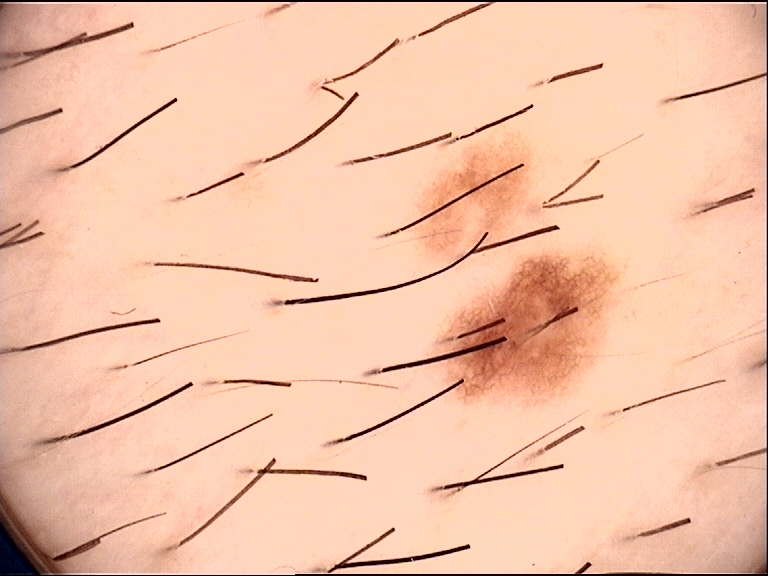imaging = dermatoscopy
diagnostic label = dysplastic junctional nevus (expert consensus)